A dermatoscopic image of a skin lesion:
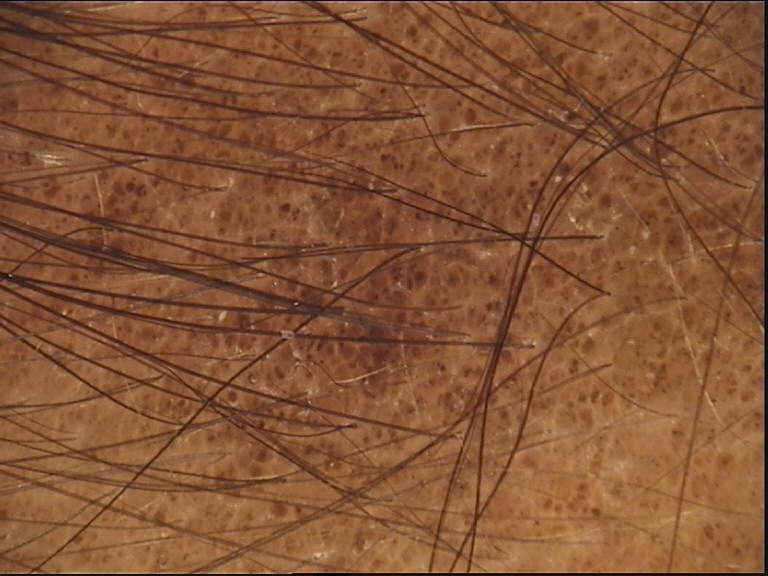diagnosis: congenital compound nevus (expert consensus).